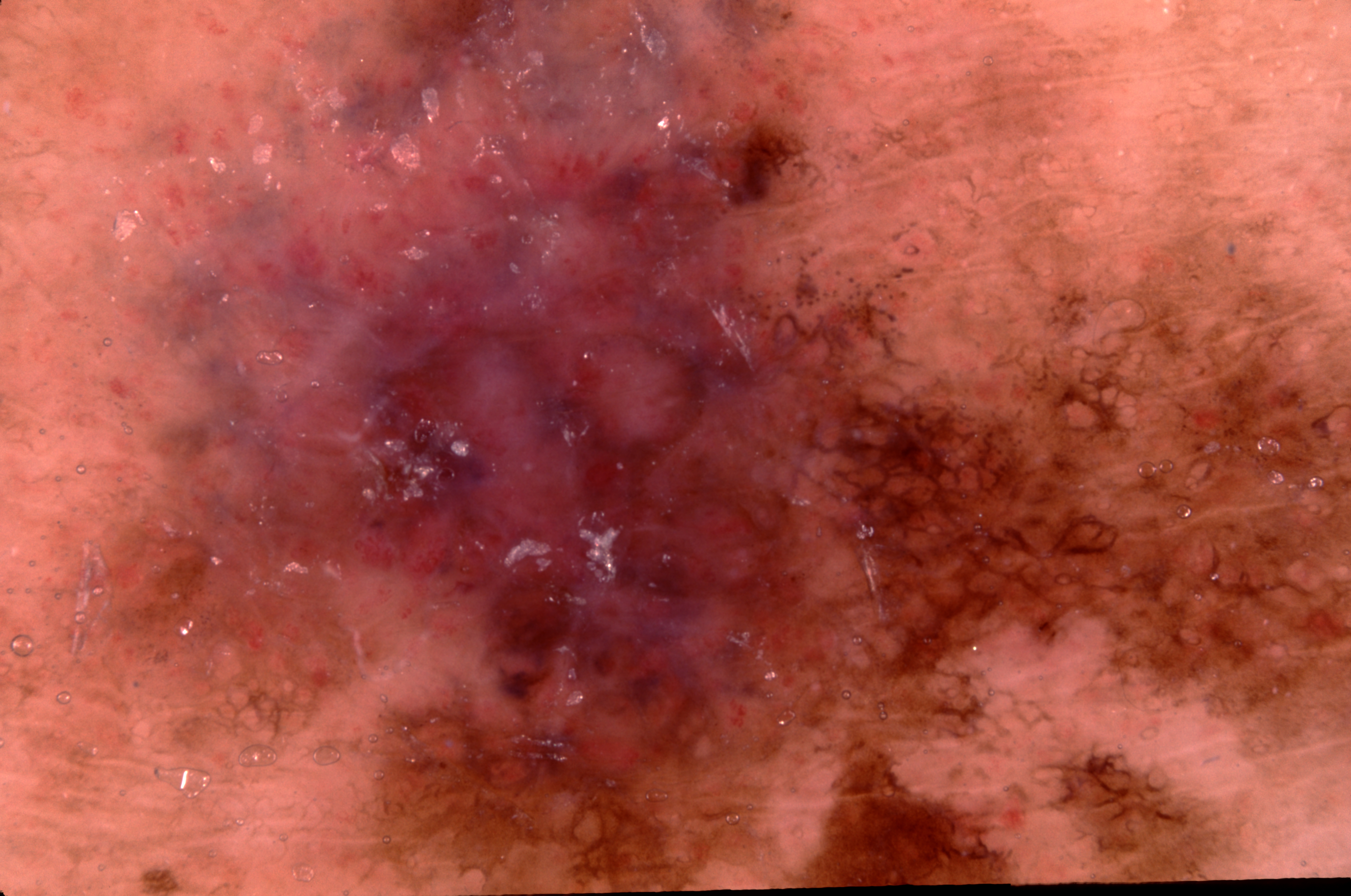A male subject approximately 75 years of age.
A dermatoscopic image of a skin lesion.
On dermoscopy, the lesion shows pigment network.
The lesion extends across the full dermoscopic field.
Biopsy-confirmed as a melanoma.